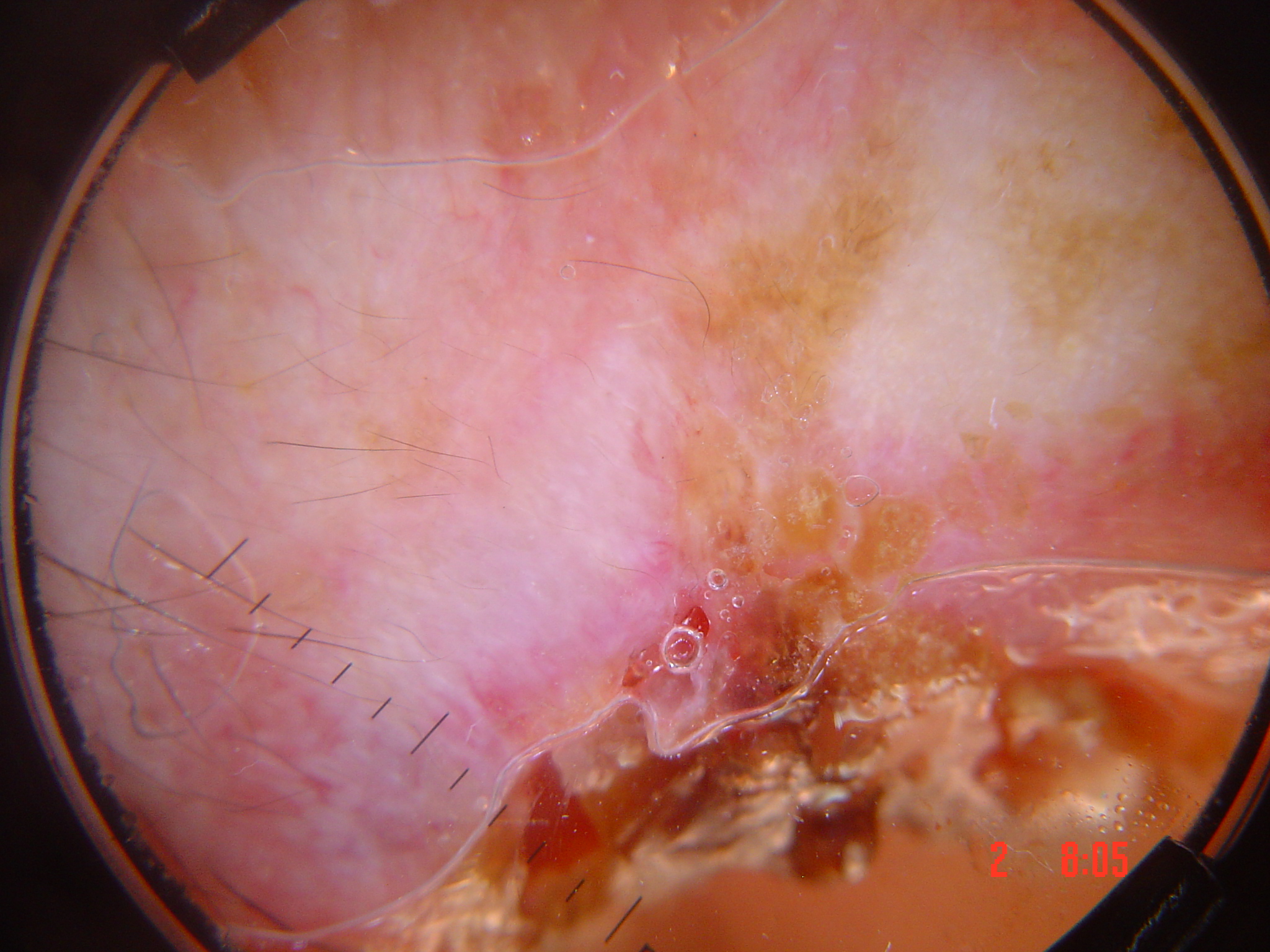Histopathologically confirmed as a squamous cell carcinoma.